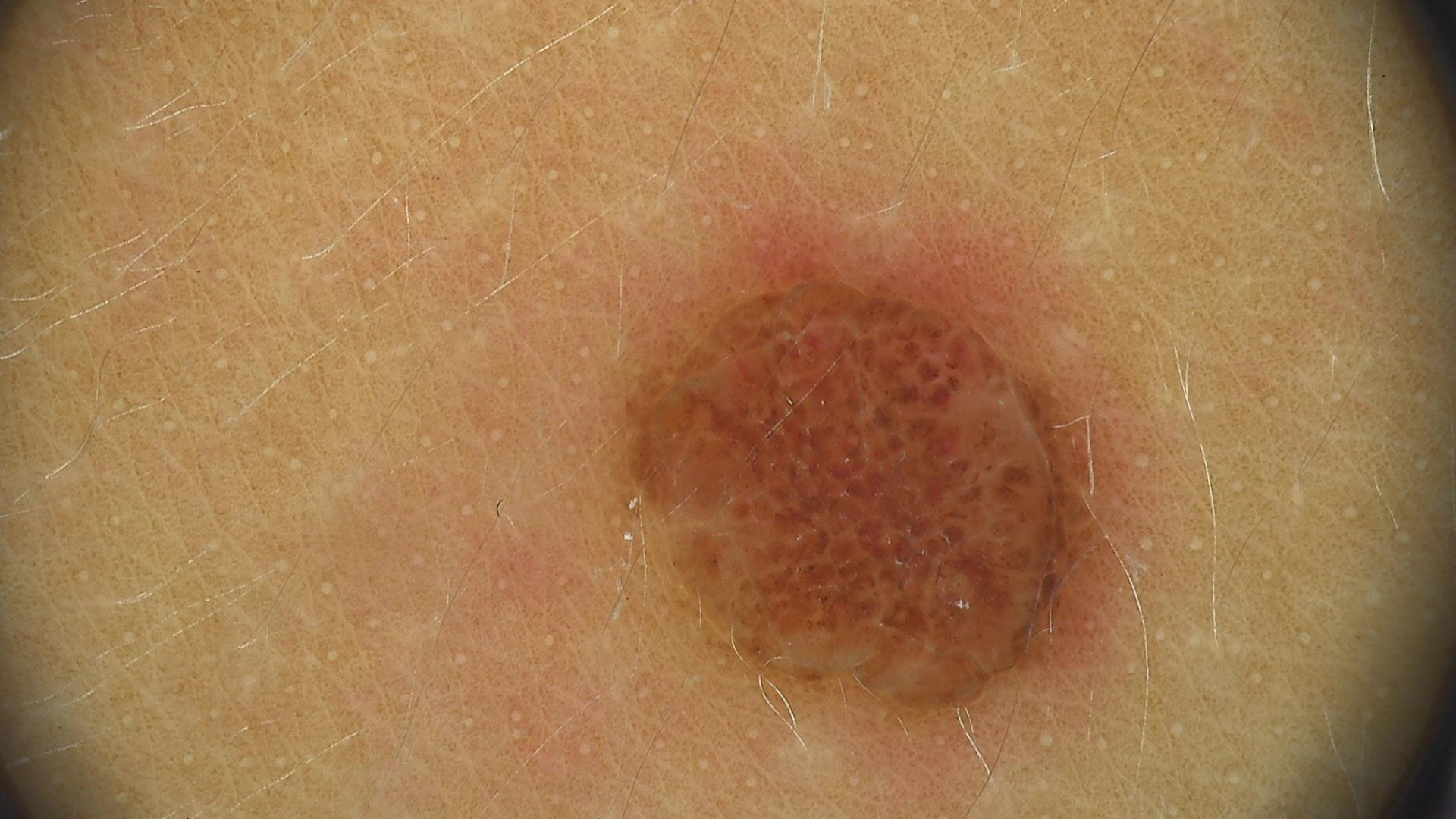Impression:
Consistent with a banal lesion — a dermal nevus.